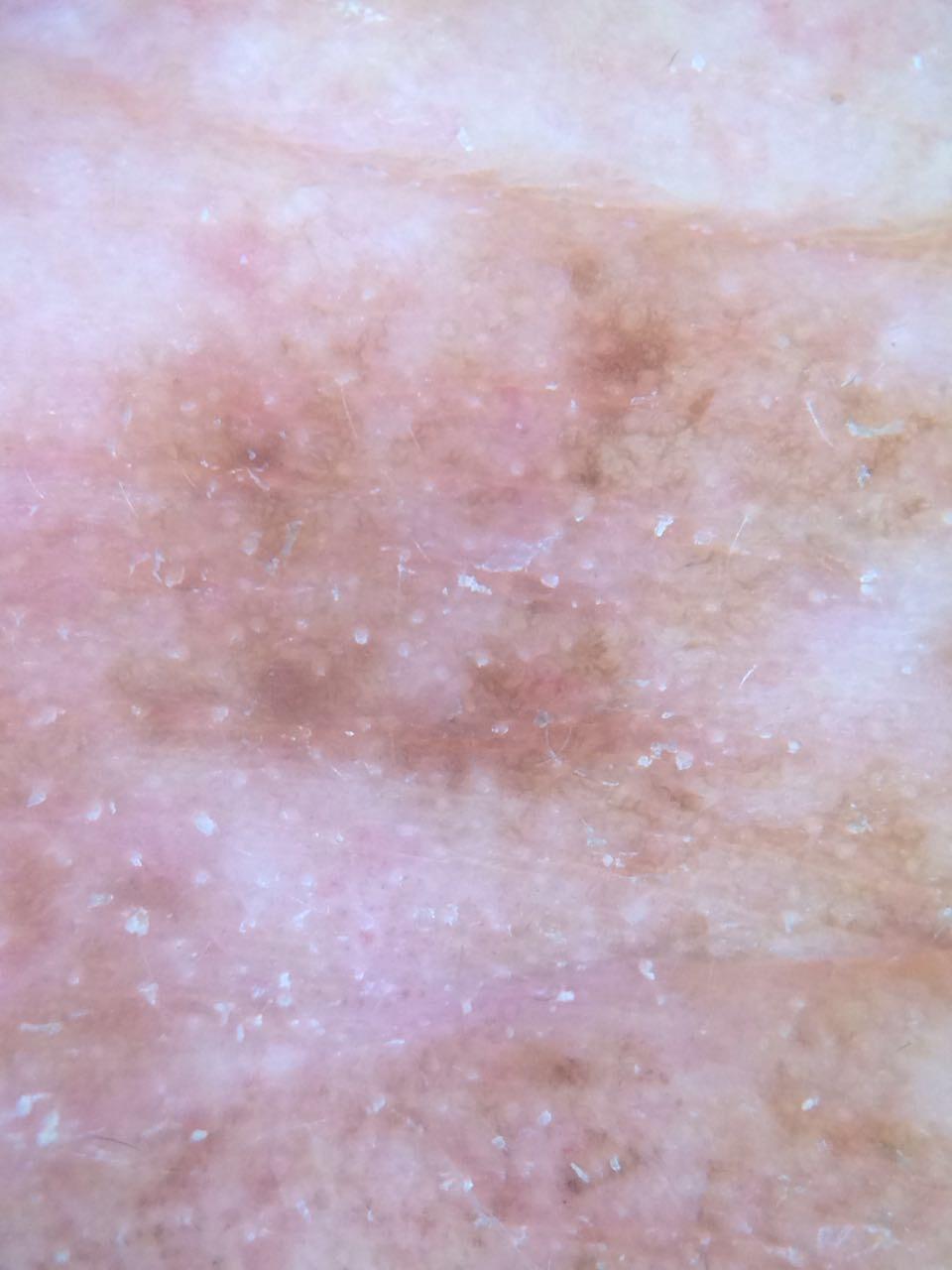Clinical context:
A male subject aged around 70. Contact-polarized dermoscopy of a skin lesion.
Conclusion:
Histopathological examination showed a melanoma.